A clinical photograph of a skin lesion. A patient aged 36 — 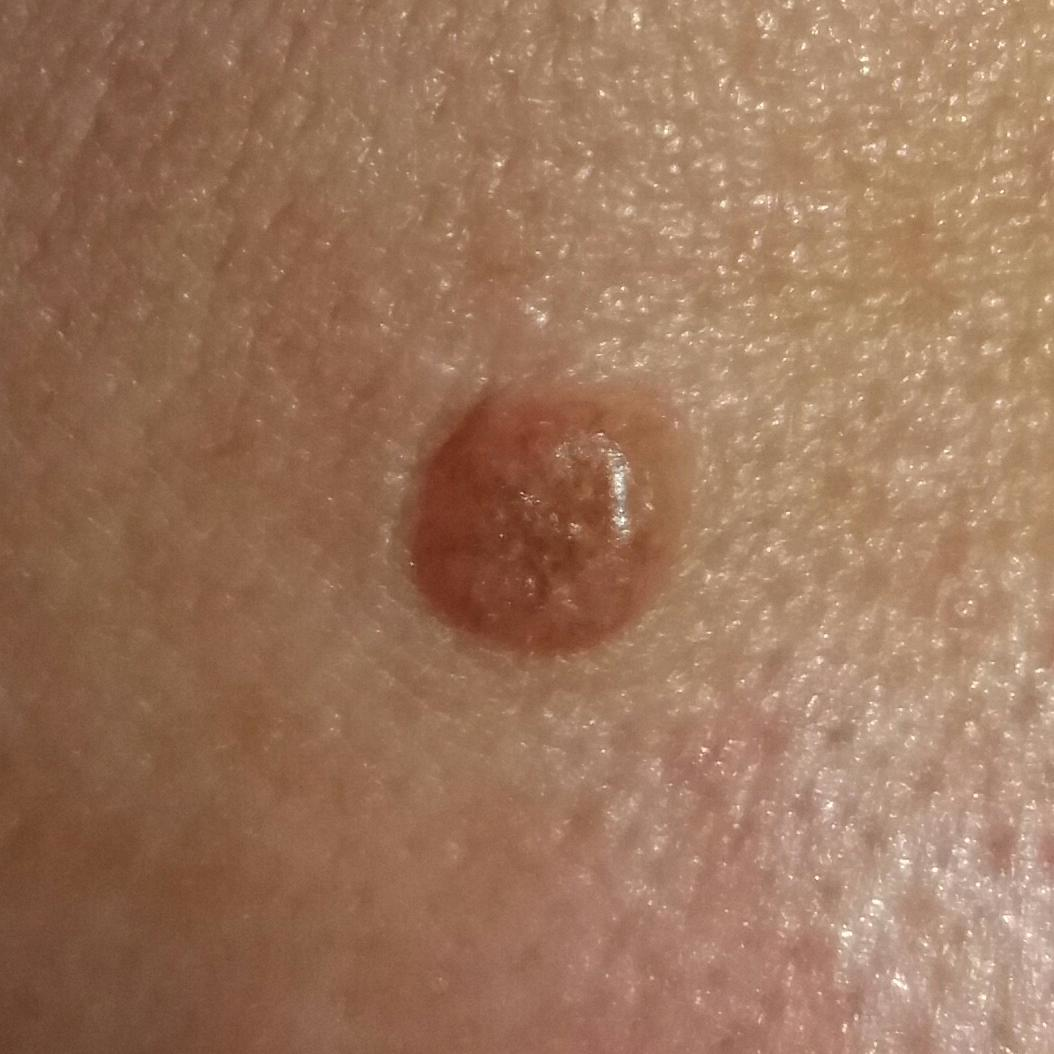| key | value |
|---|---|
| region | a lip |
| impression | nevus (clinical consensus) |